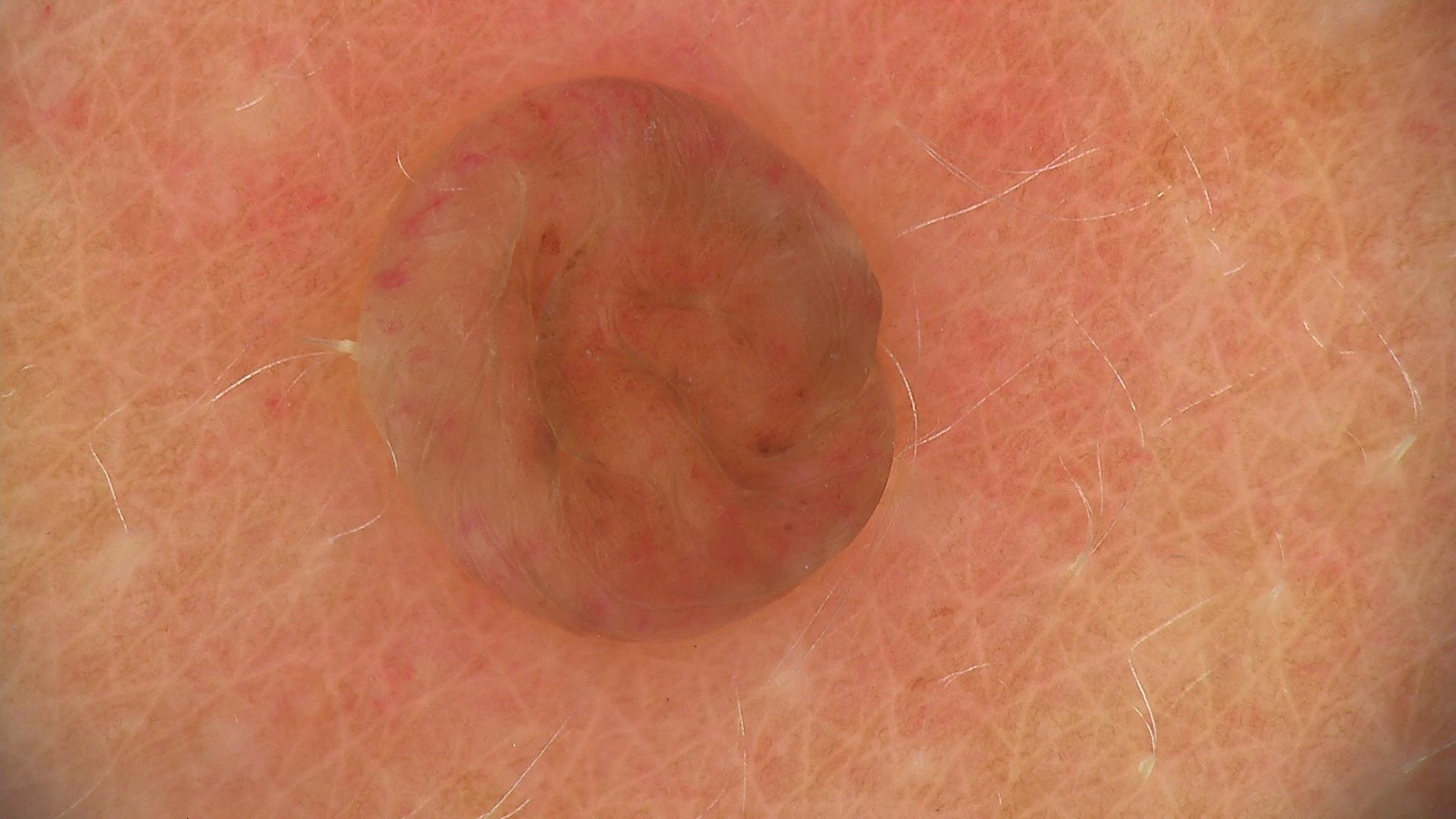modality: dermoscopy
subtype: banal
diagnostic label: dermal nevus (expert consensus)